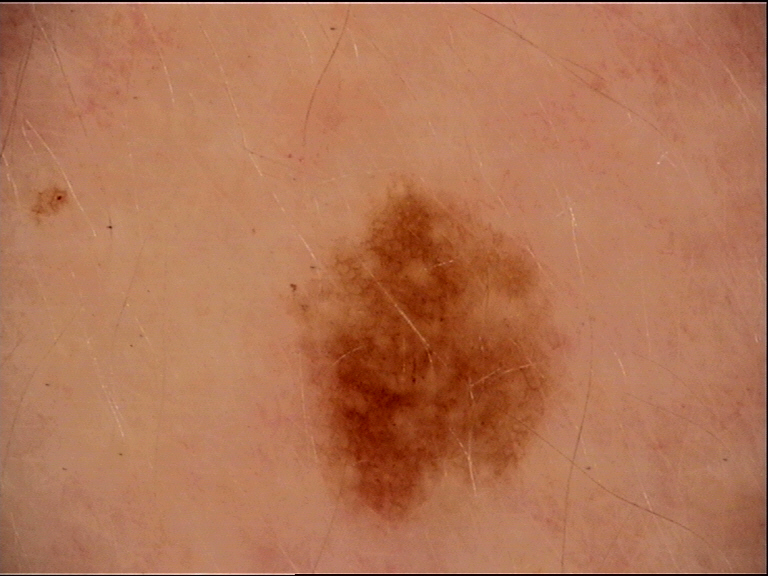label: dysplastic junctional nevus (expert consensus)